This is a close-up image · the affected area is the arm — 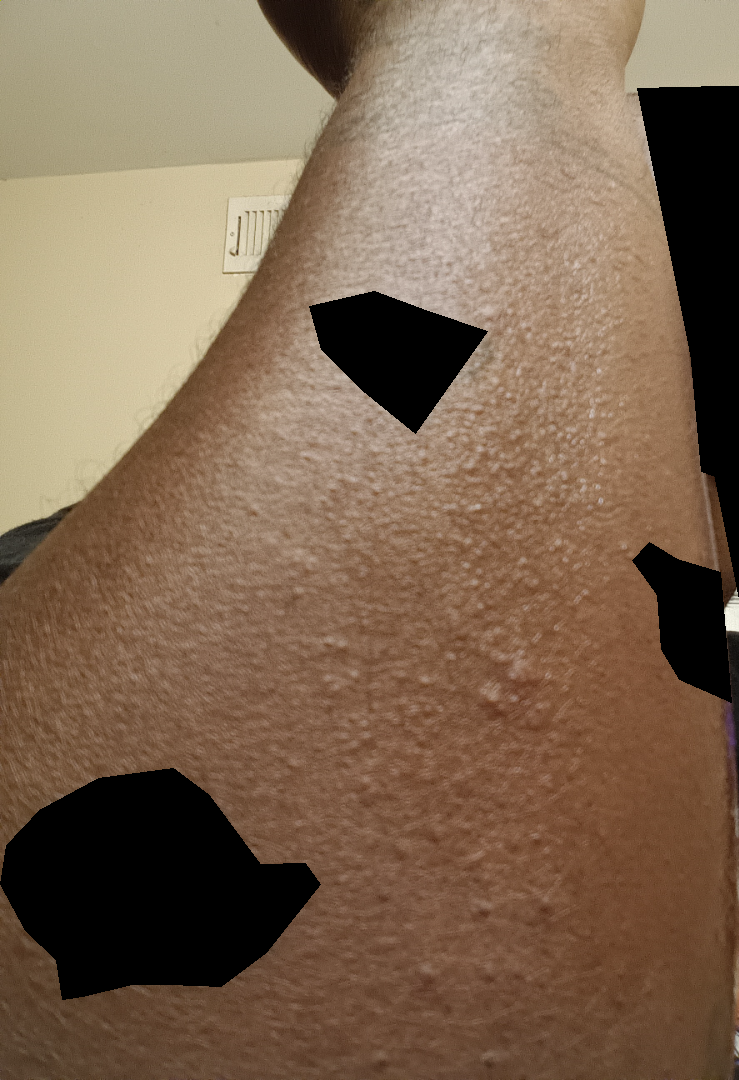Clinical context: The condition has been present for about one day. The patient considered this a rash. Fitzpatrick V. Symptoms reported: itching. Assessment: The reviewing clinician's impression was: Lichen spinulosus (possible); Eczema (possible); Keratosis pilaris (lower probability).